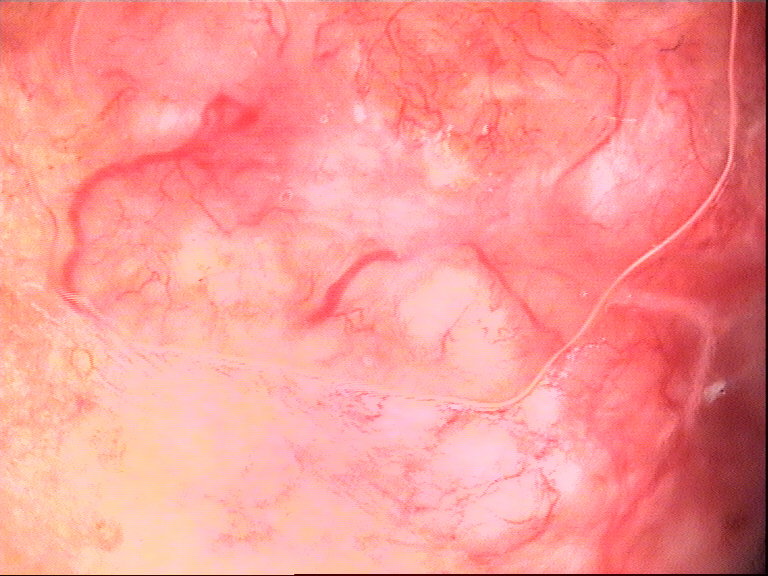A dermoscopic close-up of a skin lesion.
Confirmed on histopathology as a basal cell carcinoma.